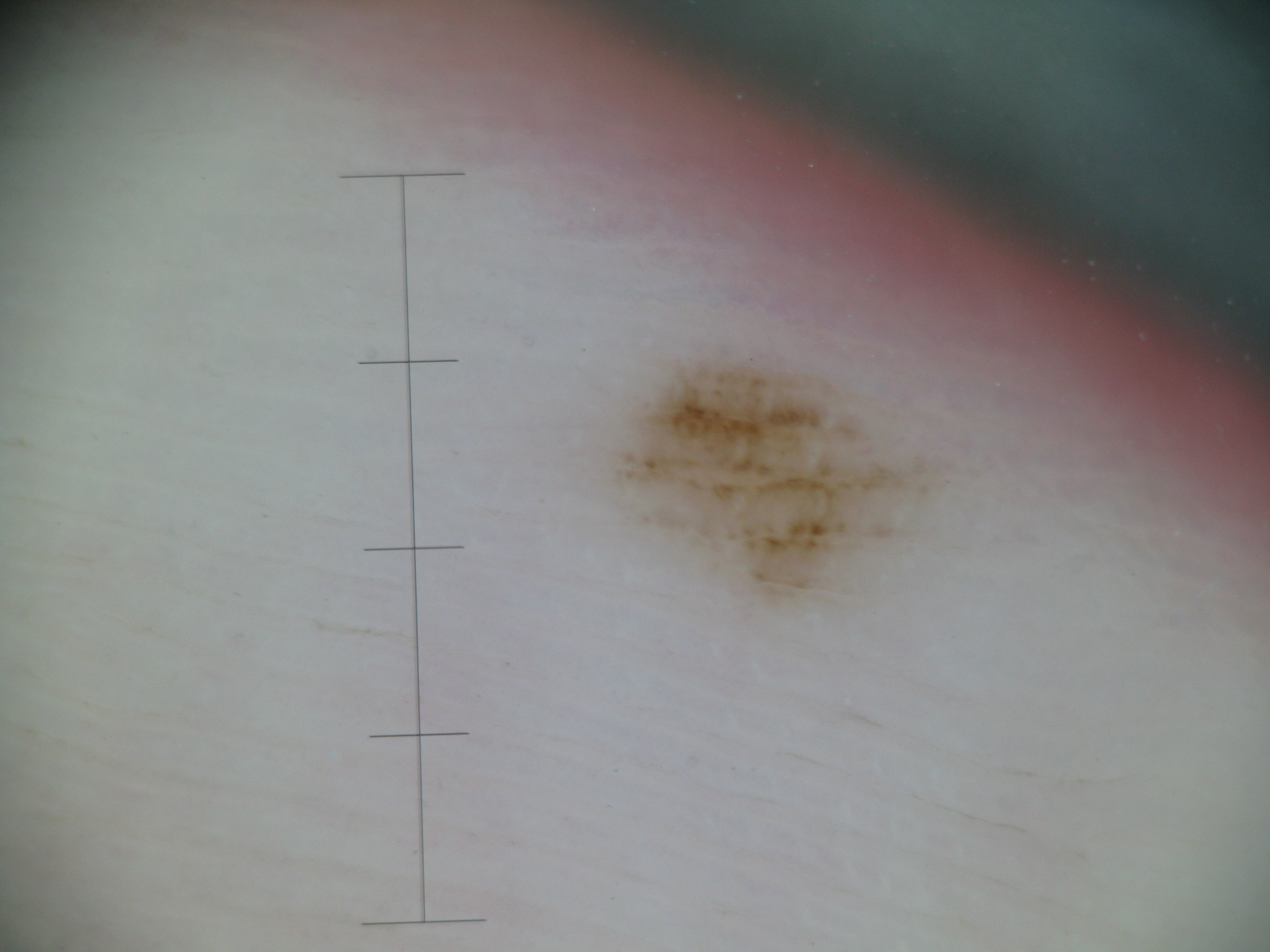Findings: A dermoscopic photograph of a skin lesion. The morphology is that of a banal lesion. Impression: The diagnostic label was an acral junctional nevus.